A dermatoscopic image of a skin lesion: 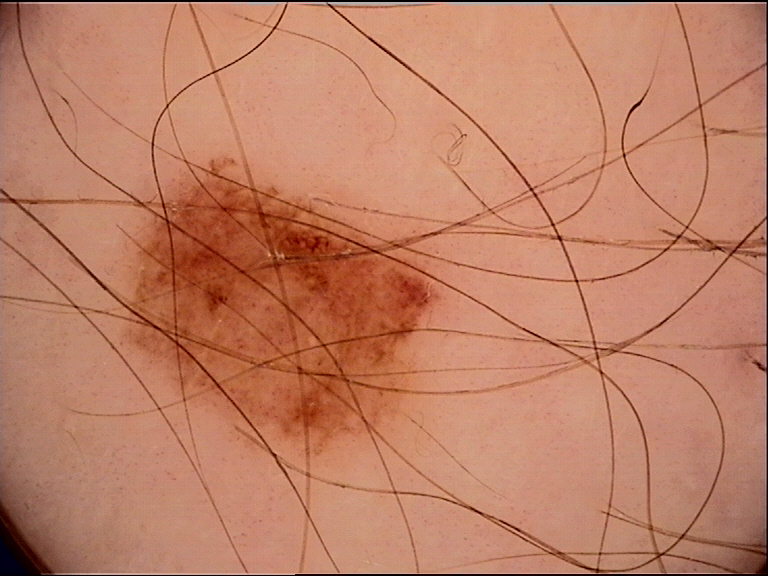Classified as a benign lesion — a dysplastic junctional nevus.